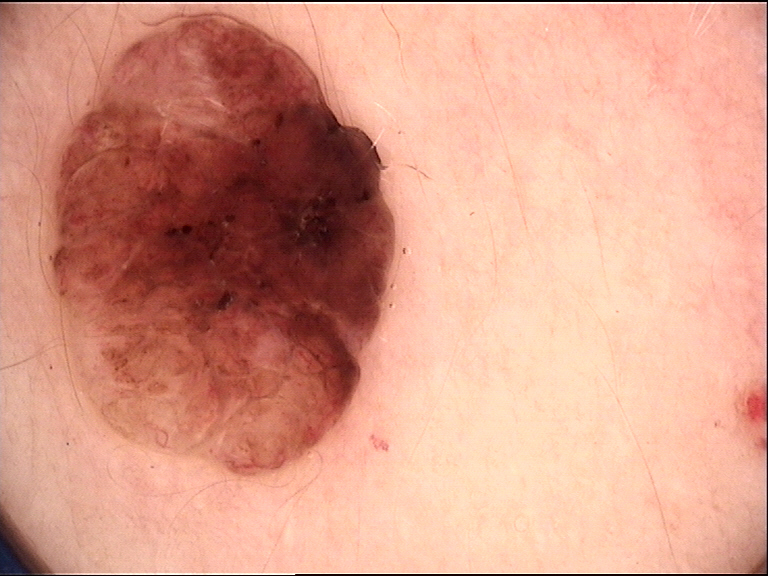| key | value |
|---|---|
| image type | dermatoscopy |
| subtype | banal |
| diagnosis | dermal nevus (expert consensus) |